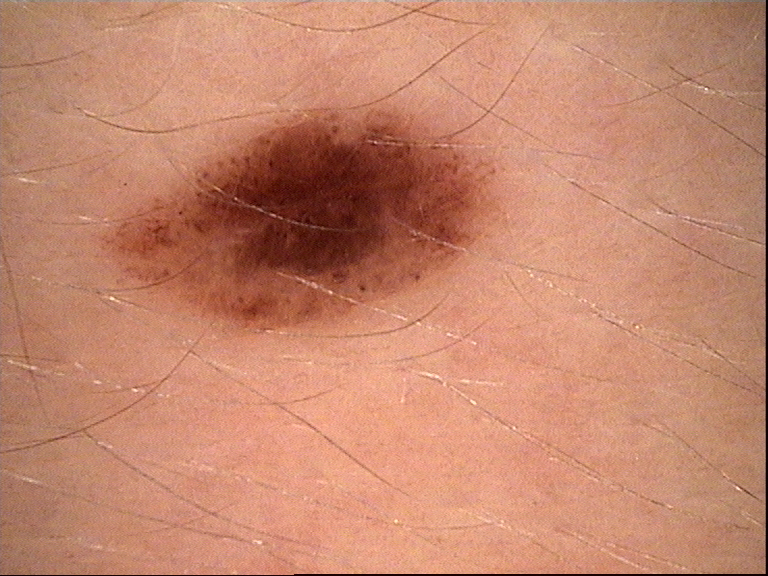A dermatoscopic image of a skin lesion.
Labeled as a dysplastic compound nevus.